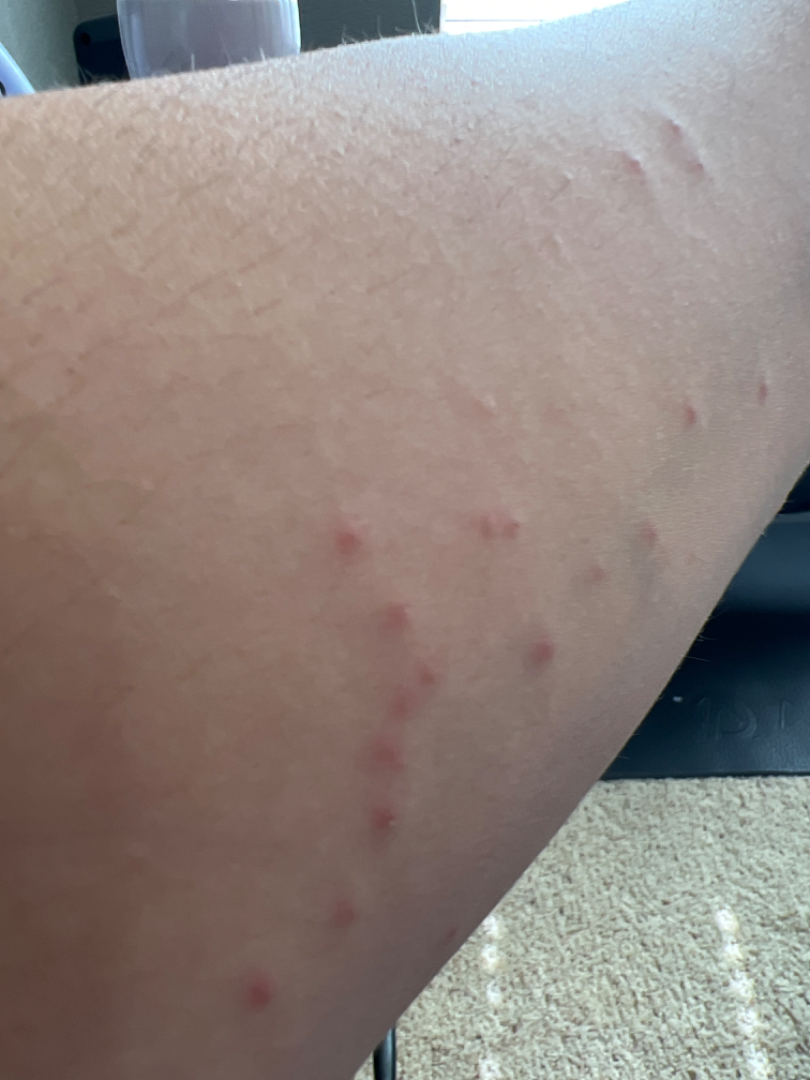| field | value |
|---|---|
| dermatologist impression | favoring Insect Bite; an alternative is Hypersensitivity; a more distant consideration is Eczema |